A skin lesion imaged with a dermatoscope: 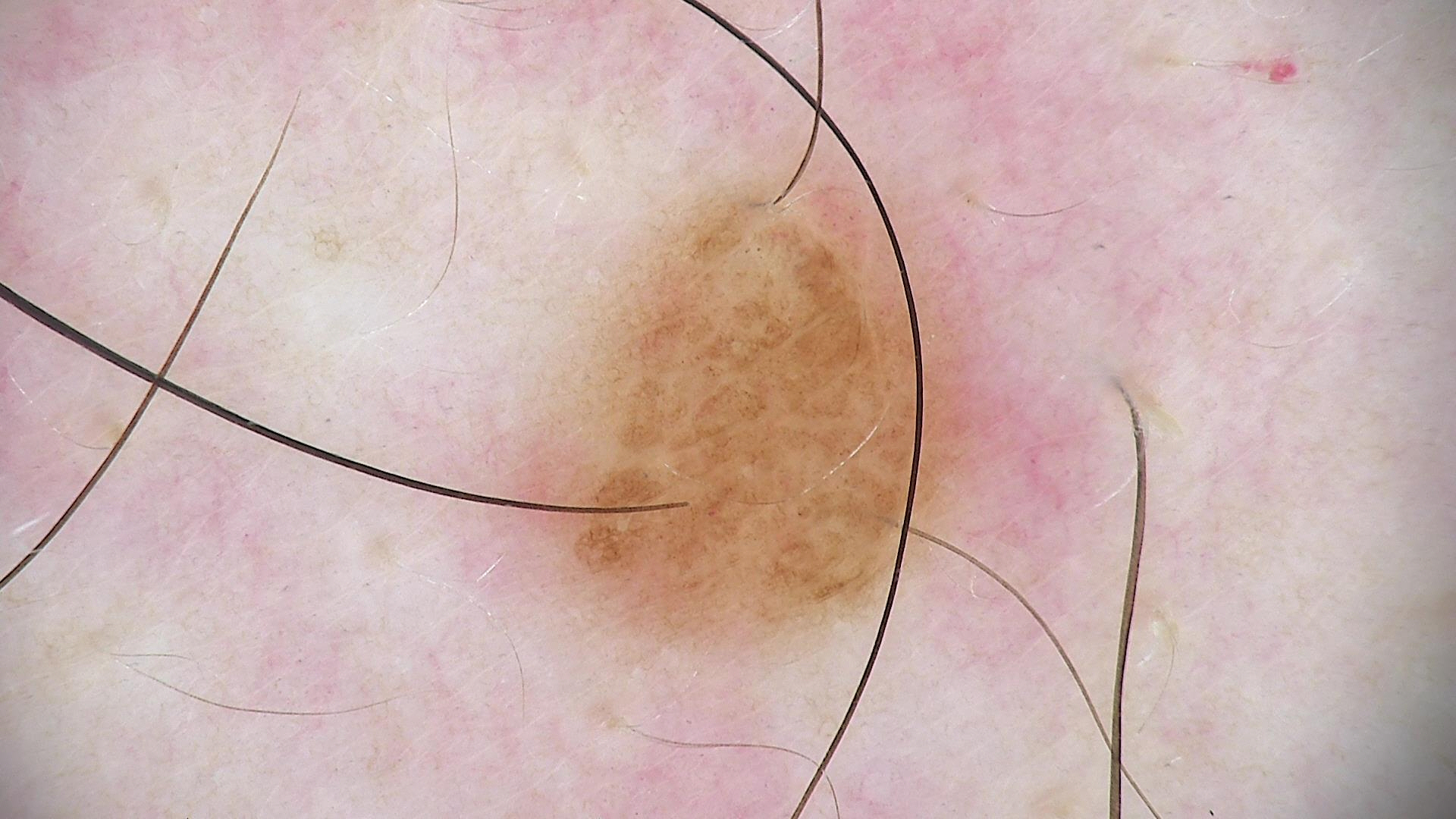Impression: Consistent with a banal lesion — a compound nevus.